A female subject in their 50s · a clinical photograph of a skin lesion · Fitzpatrick skin type III · by history, prior malignancy (patient or family), prior skin cancer (patient or family), no tobacco use, and no alcohol use — 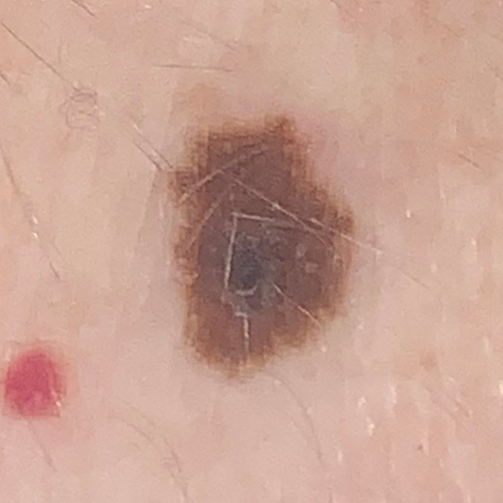{"lesion_location": "the back", "lesion_size": {"diameter_1_mm": 8.0, "diameter_2_mm": 5.0}, "symptoms": {"present": ["change in appearance", "growth"], "absent": ["itching"]}, "diagnosis": {"name": "nevus", "code": "NEV", "malignancy": "benign", "confirmation": "histopathology"}}